Dermoscopy of a skin lesion.
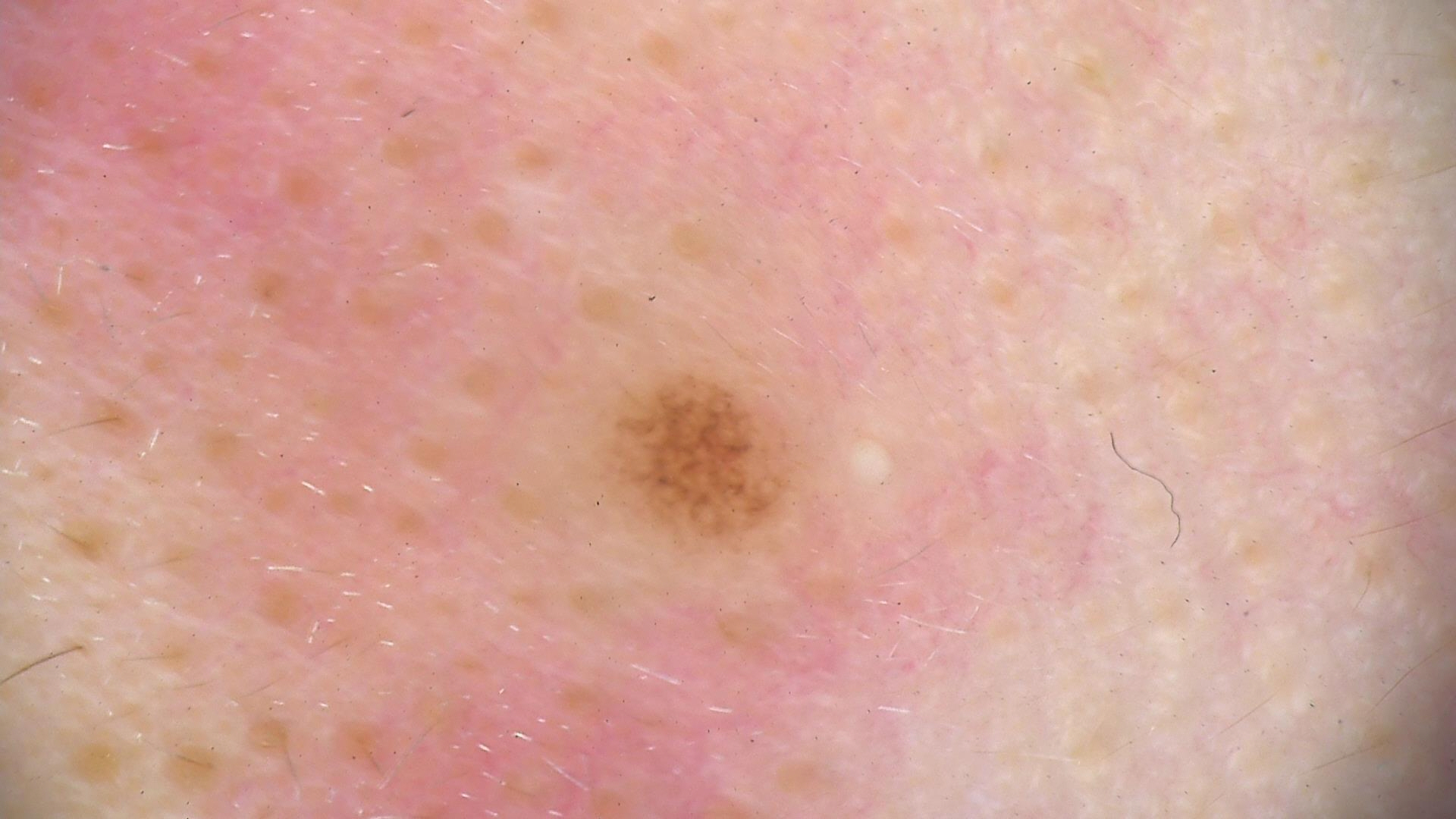category: banal | diagnostic label: compound nevus (expert consensus).